A skin lesion imaged with a dermatoscope.
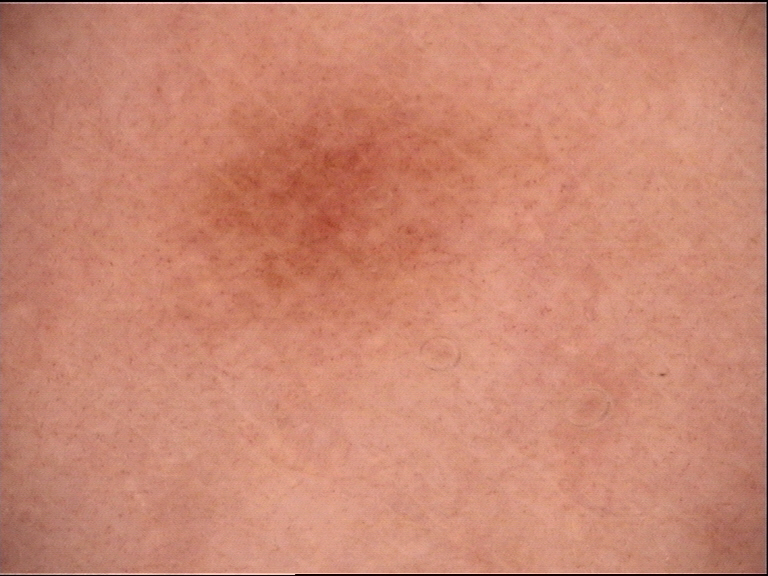{"diagnosis": {"name": "dysplastic junctional nevus", "code": "jd", "malignancy": "benign", "super_class": "melanocytic", "confirmation": "expert consensus"}}